An image taken at a distance · the patient indicates the lesion is rough or flaky, fluid-filled and raised or bumpy · the arm is involved · female patient, age 18–29 · associated systemic symptoms include mouth sores, fever, joint pain and fatigue · reported duration is one to four weeks:
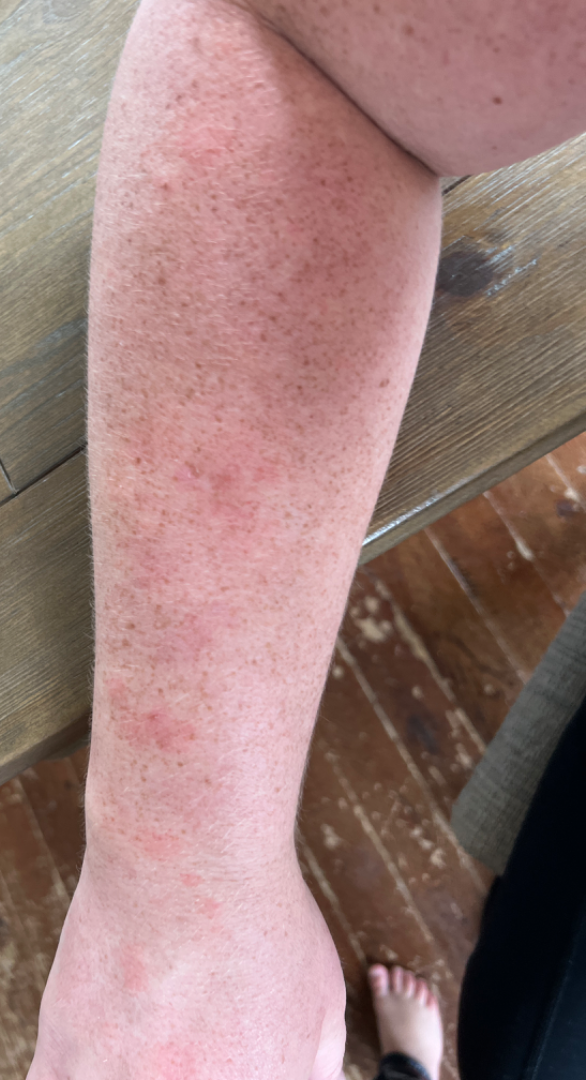On teledermatology review: the differential, in no particular order, includes Eczema, Photodermatitis, Allergic Contact Dermatitis, Lentigo, Sunburn and Acquired poikiloderma.